A dermoscopic image of a skin lesion.
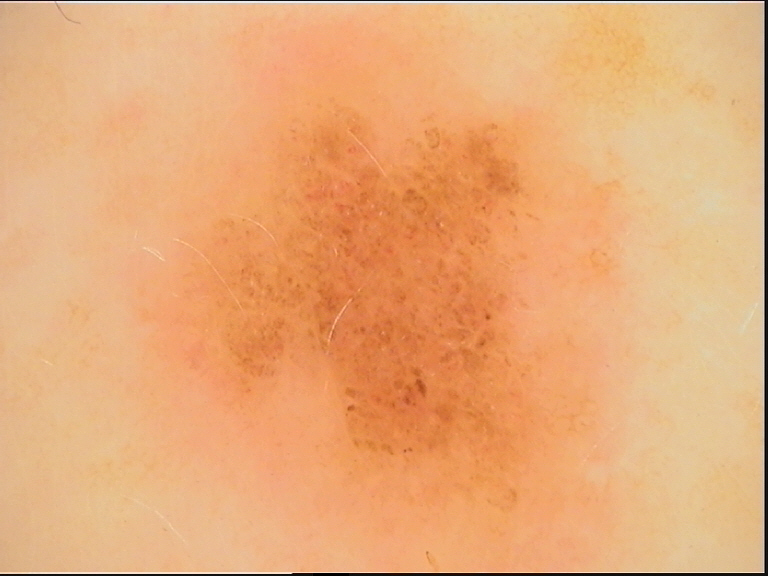Diagnosed as a dysplastic junctional nevus.